An image taken at an angle; the condition has been present for one to four weeks; the back of the hand, arm and leg are involved; texture is reported as rough or flaky; the lesion is associated with itching: 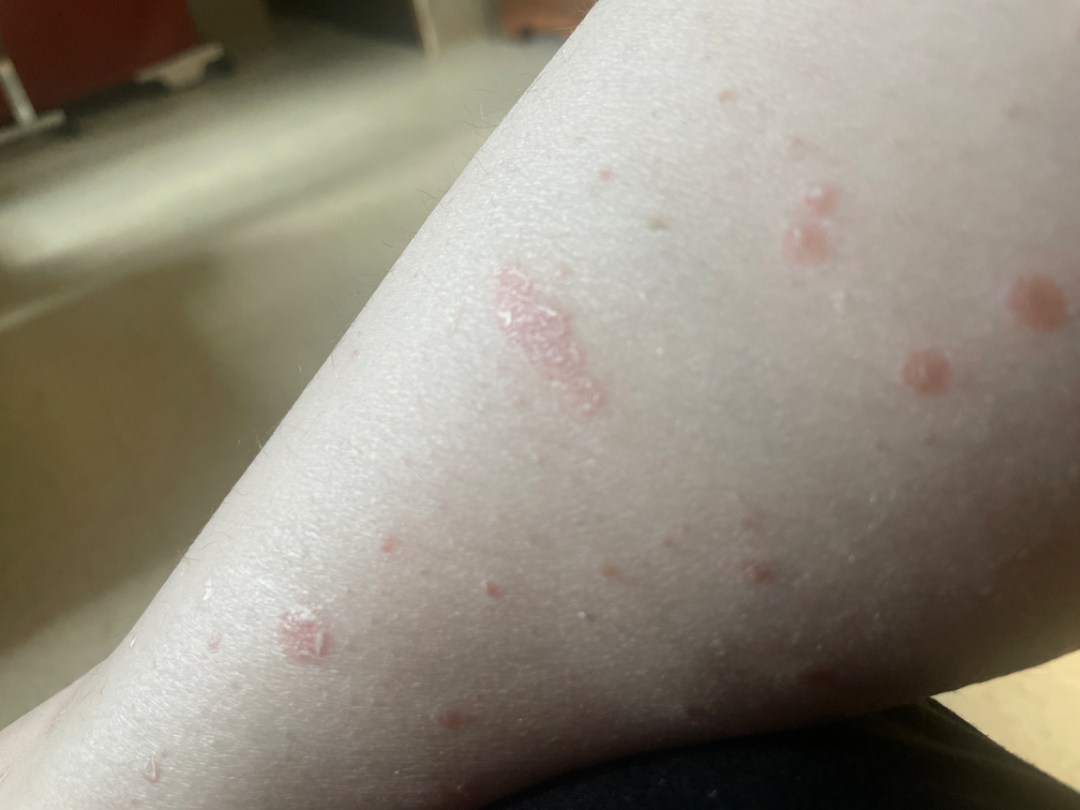Assessment:
Most consistent with Psoriasis.